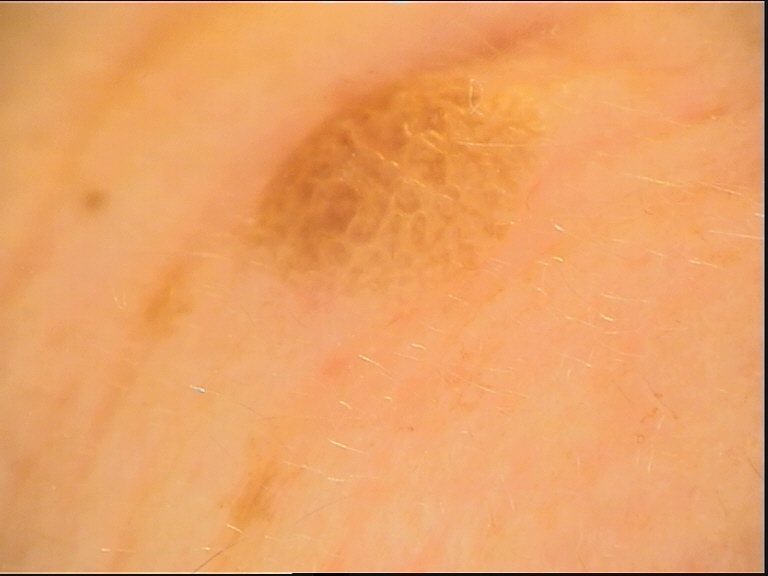This is a keratinocytic lesion. Diagnosed as a seborrheic keratosis.